A skin lesion imaged with a dermatoscope.
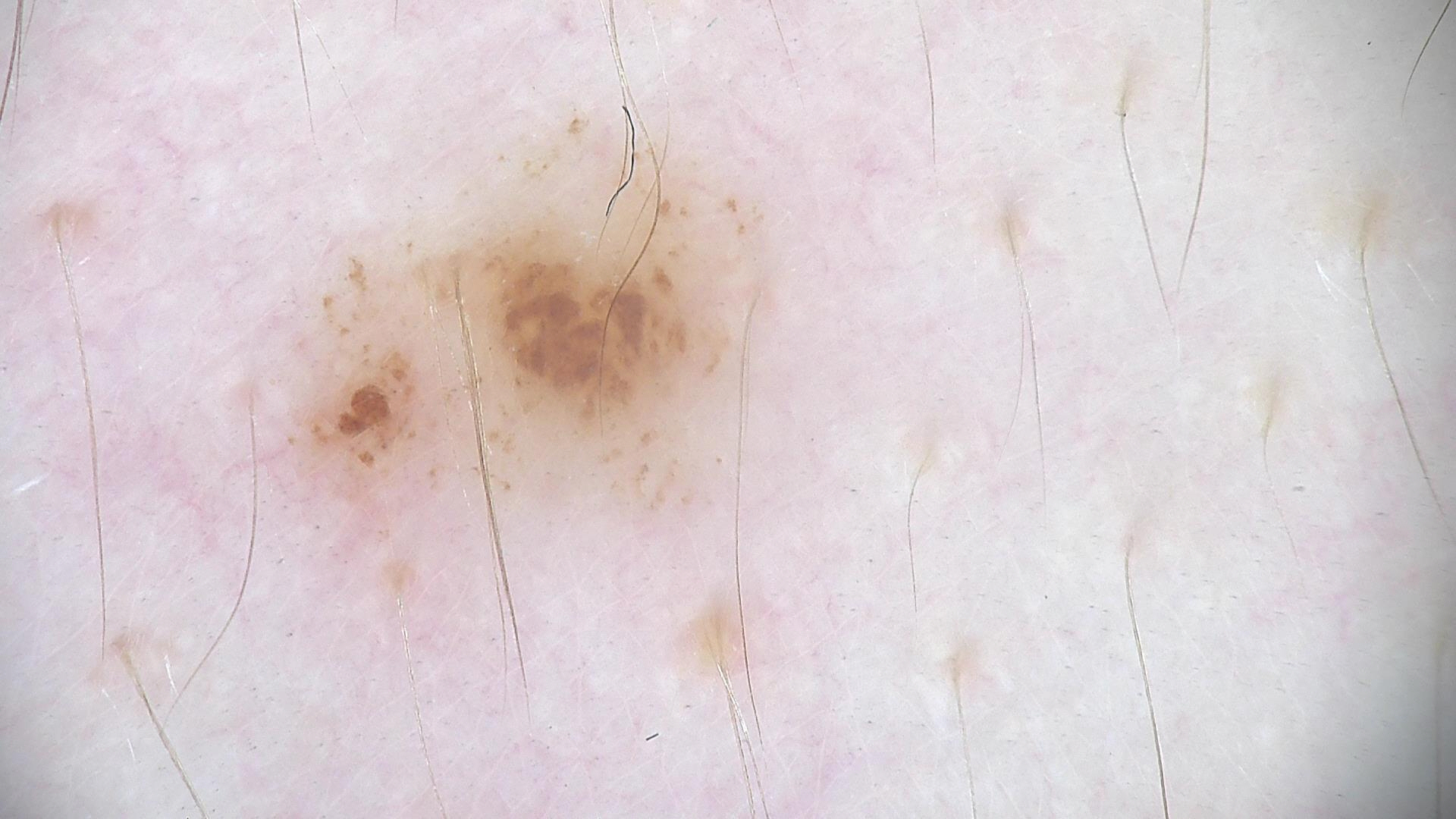The diagnosis was a dysplastic junctional nevus.